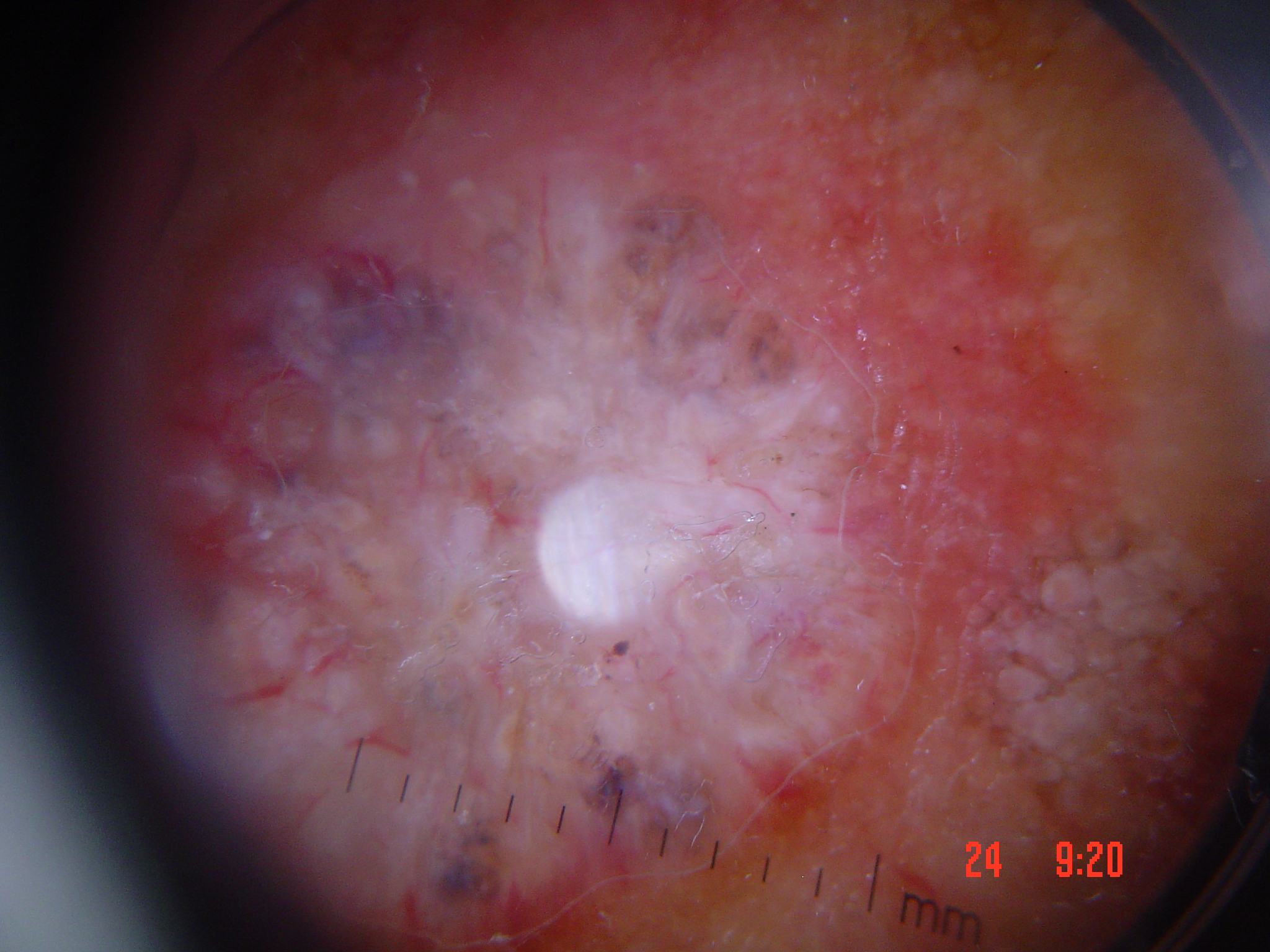Summary:
Dermoscopy of a skin lesion.
Conclusion:
Confirmed on histopathology as a malignant, keratinocytic lesion — a basal cell carcinoma.